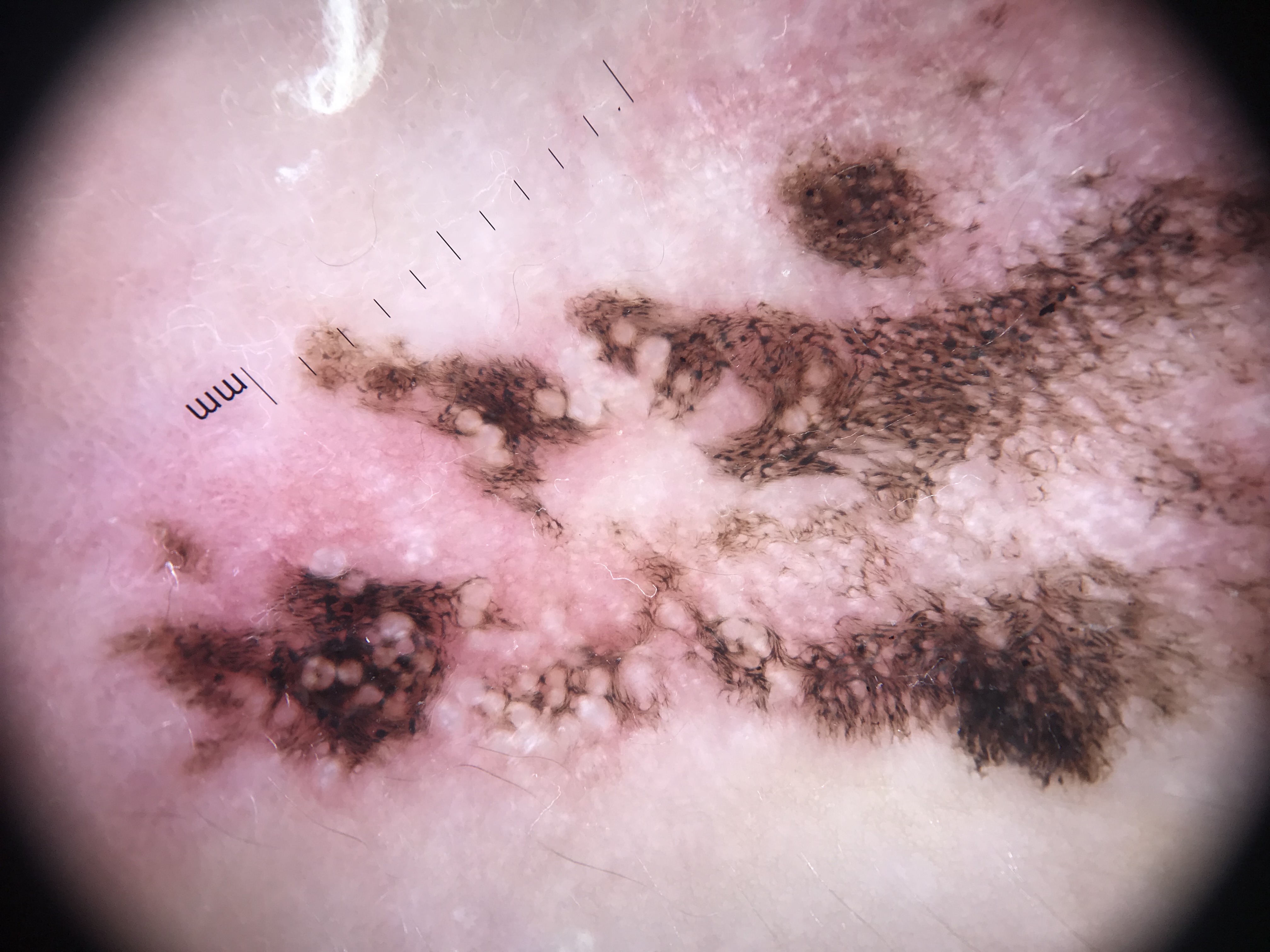{
  "diagnosis": {
    "name": "melanoma",
    "code": "mel",
    "malignancy": "malignant",
    "super_class": "melanocytic",
    "confirmation": "histopathology"
  }
}